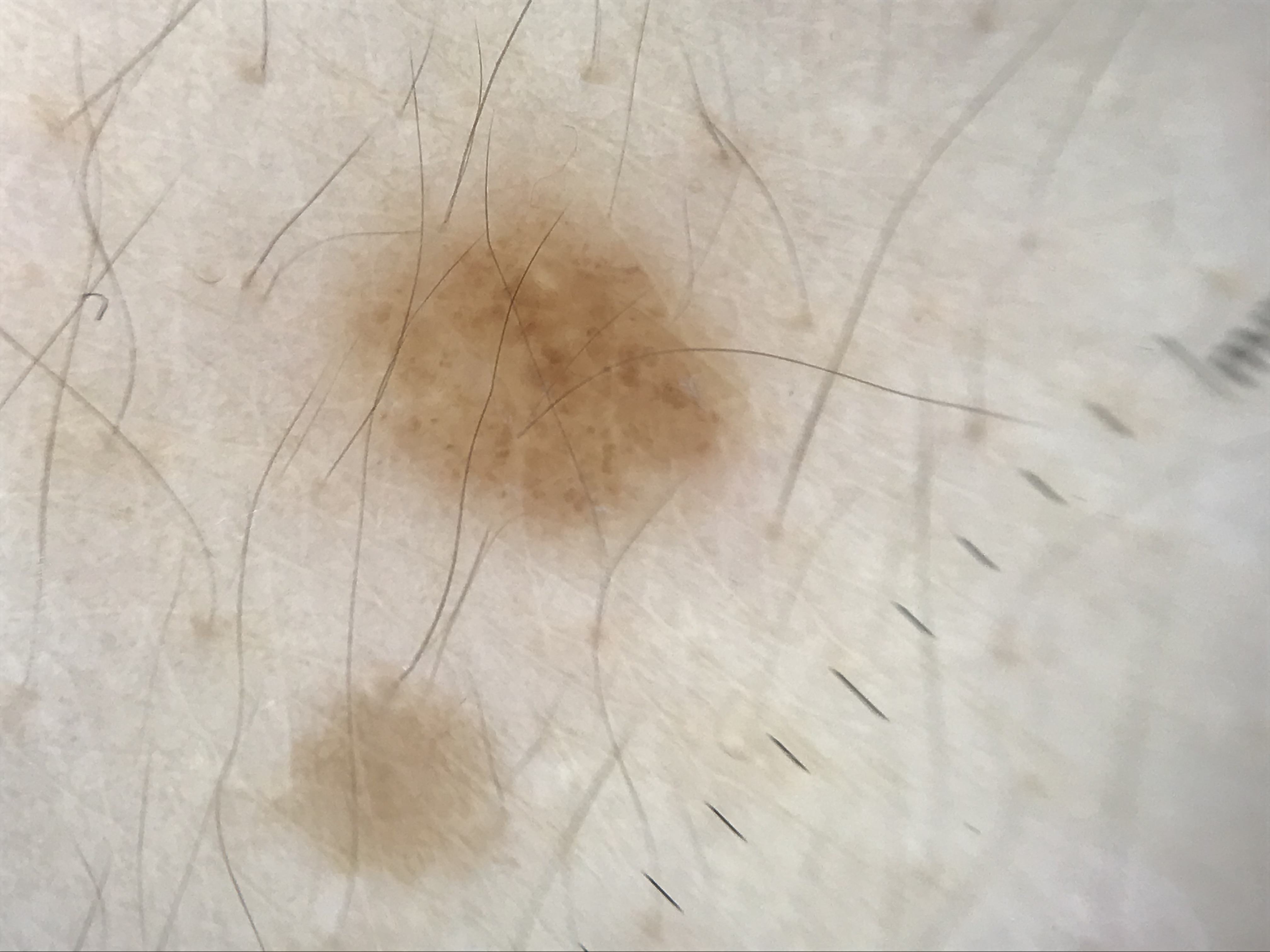image type = dermatoscopy
diagnosis = junctional nevus (expert consensus)